This is a close-up image — 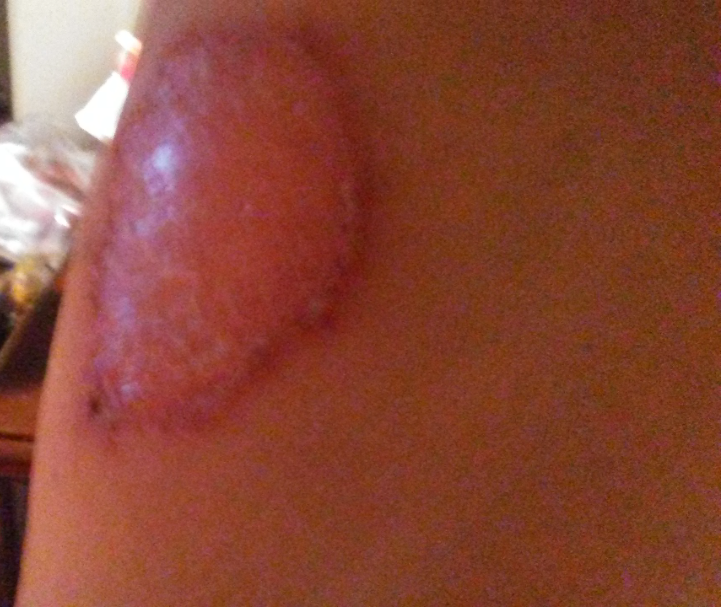Findings:
One reviewing dermatologist: most likely Ecthyma; possibly Porokeratosis; also on the differential is Eczema.